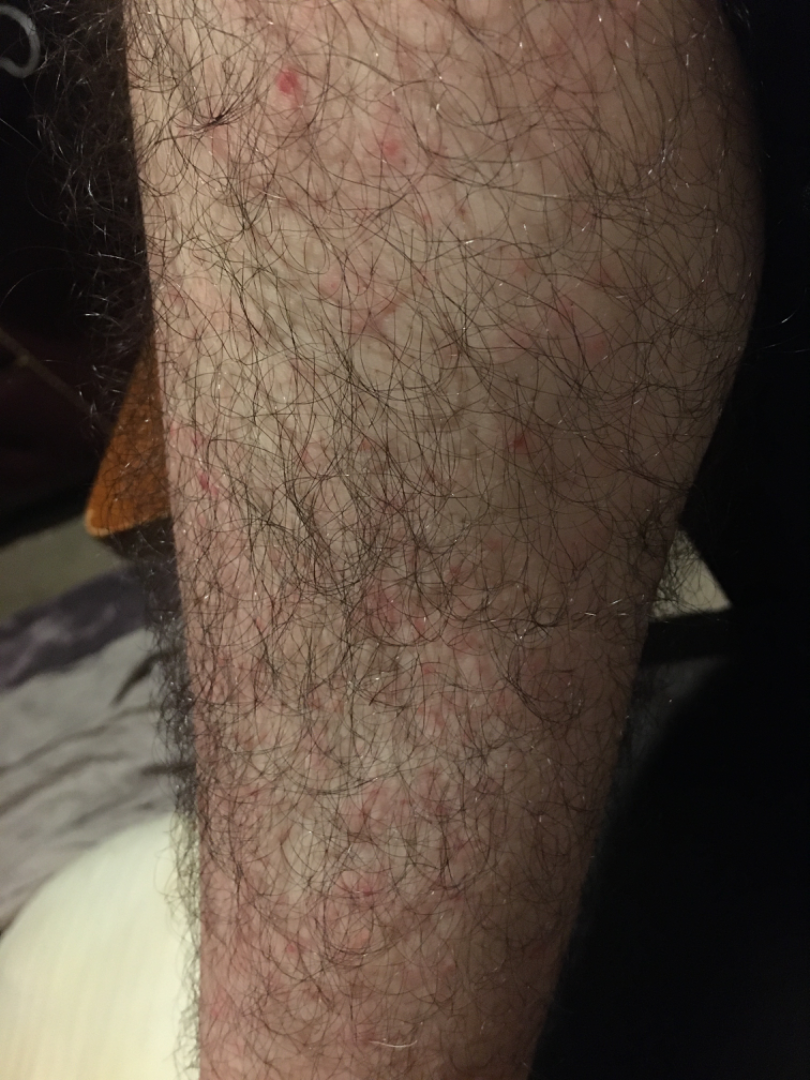{"patient_category": "a rash", "duration": "less than one week", "shot_type": "at an angle", "body_site": ["palm", "back of the torso", "top or side of the foot", "front of the torso", "leg", "sole of the foot", "head or neck", "arm", "back of the hand"], "skin_tone": {"fitzpatrick": "II", "monk_skin_tone": [2, 3]}, "differential": {"tied_lead": ["Folliculitis", "Eczema", "Allergic Contact Dermatitis"]}}